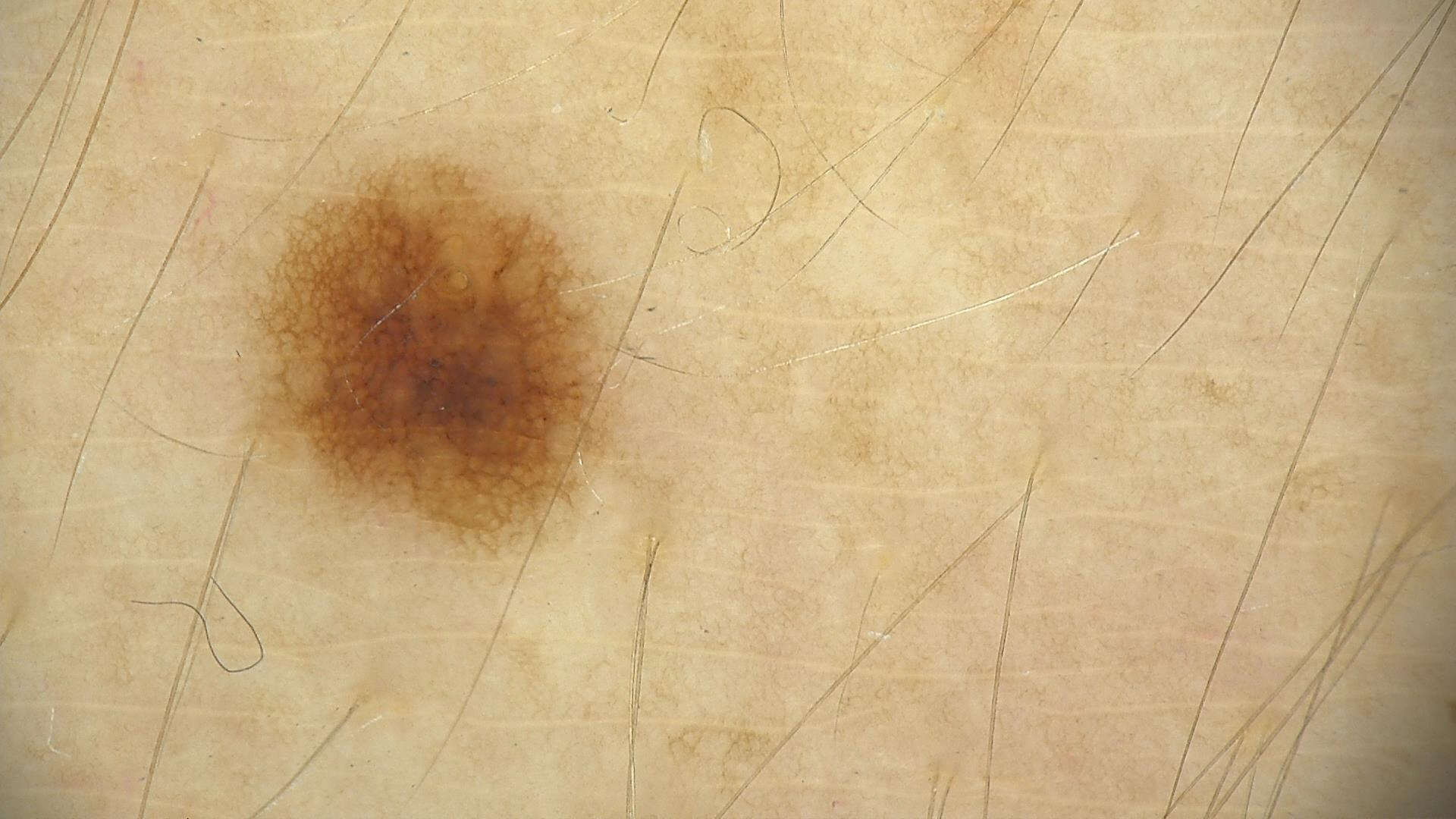modality: dermoscopy; assessment: dysplastic junctional nevus (expert consensus).